A dermoscopic photograph of a skin lesion.
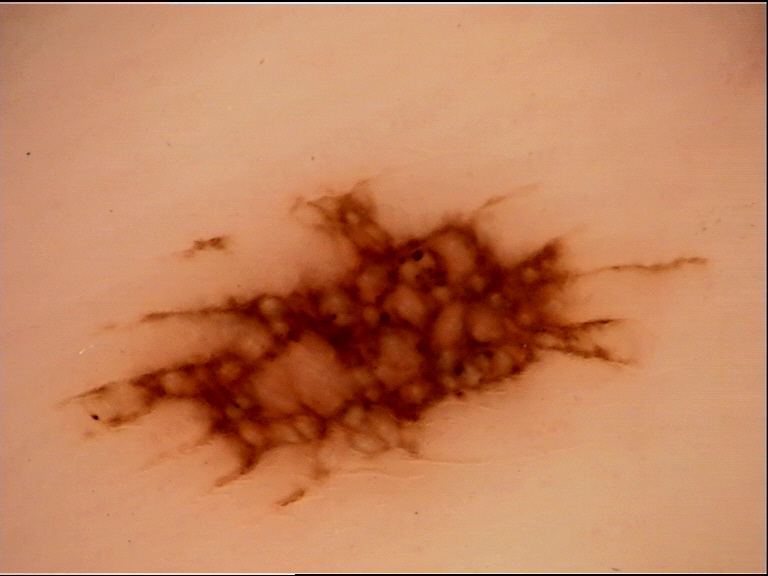The diagnostic label was an acral junctional nevus.